A dermatoscopic image of a skin lesion: 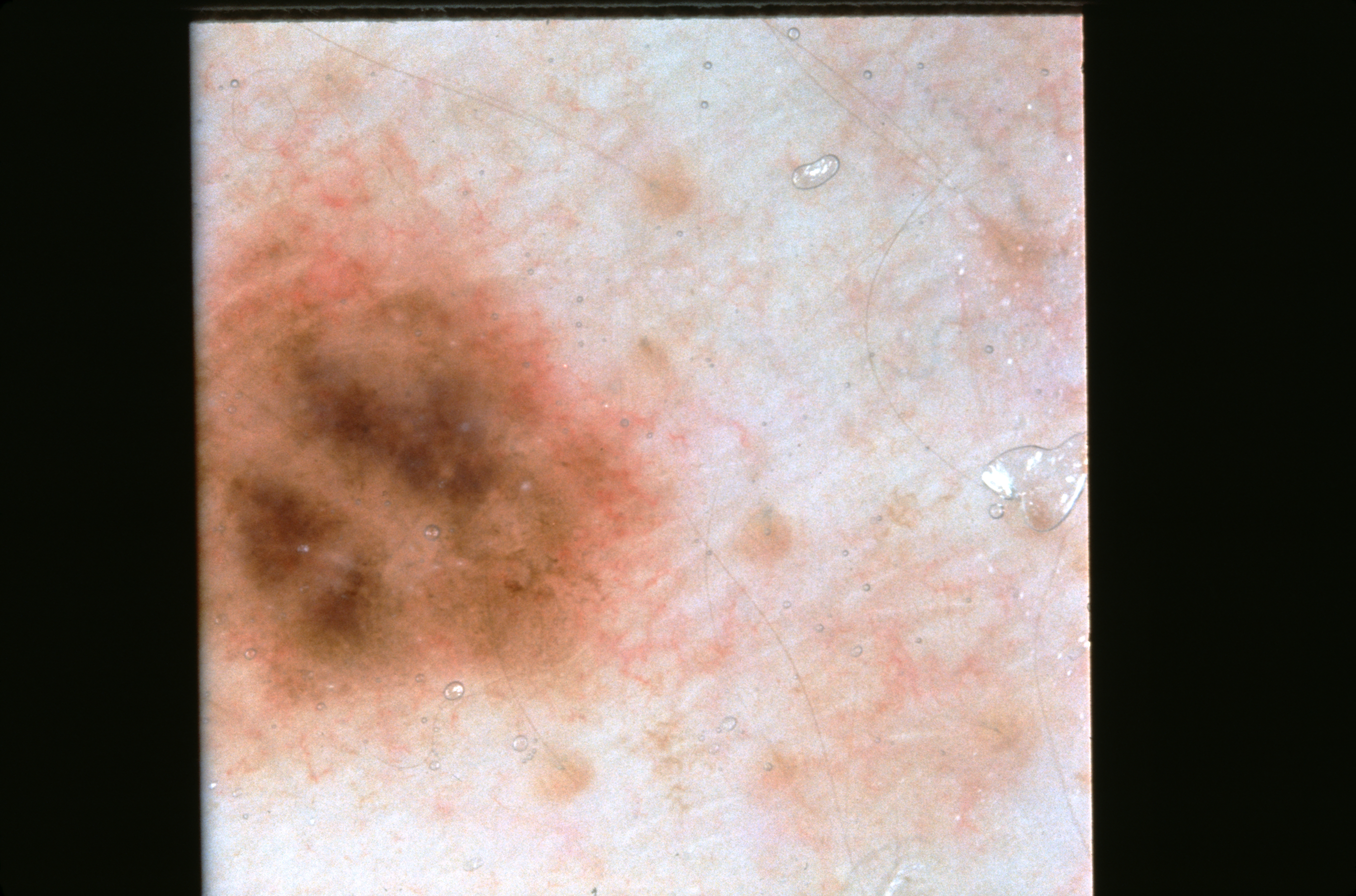  lesion_location:
    bbox_xyxy:
      - 199
      - 113
      - 701
      - 795
  diagnosis:
    name: melanocytic nevus
    malignancy: benign
    lineage: melanocytic
    provenance: clinical